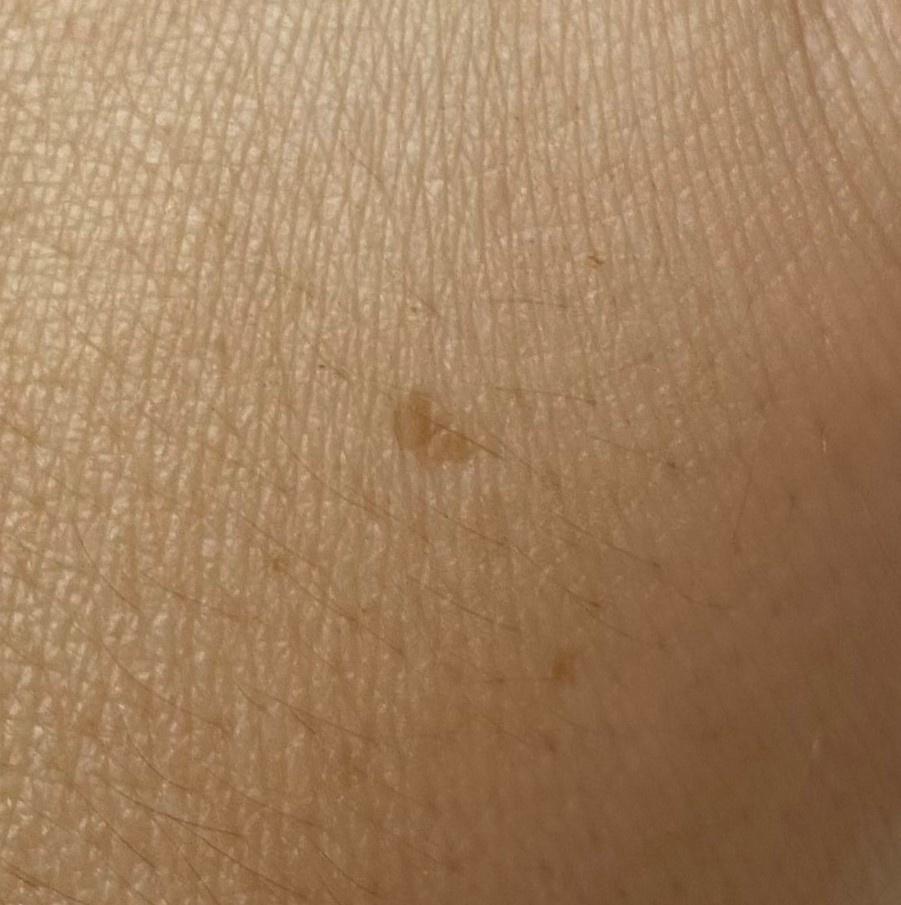A female subject roughly 35 years of age.
Fitzpatrick phototype II.
Consistent with a benign lesion — a solar lentigo.